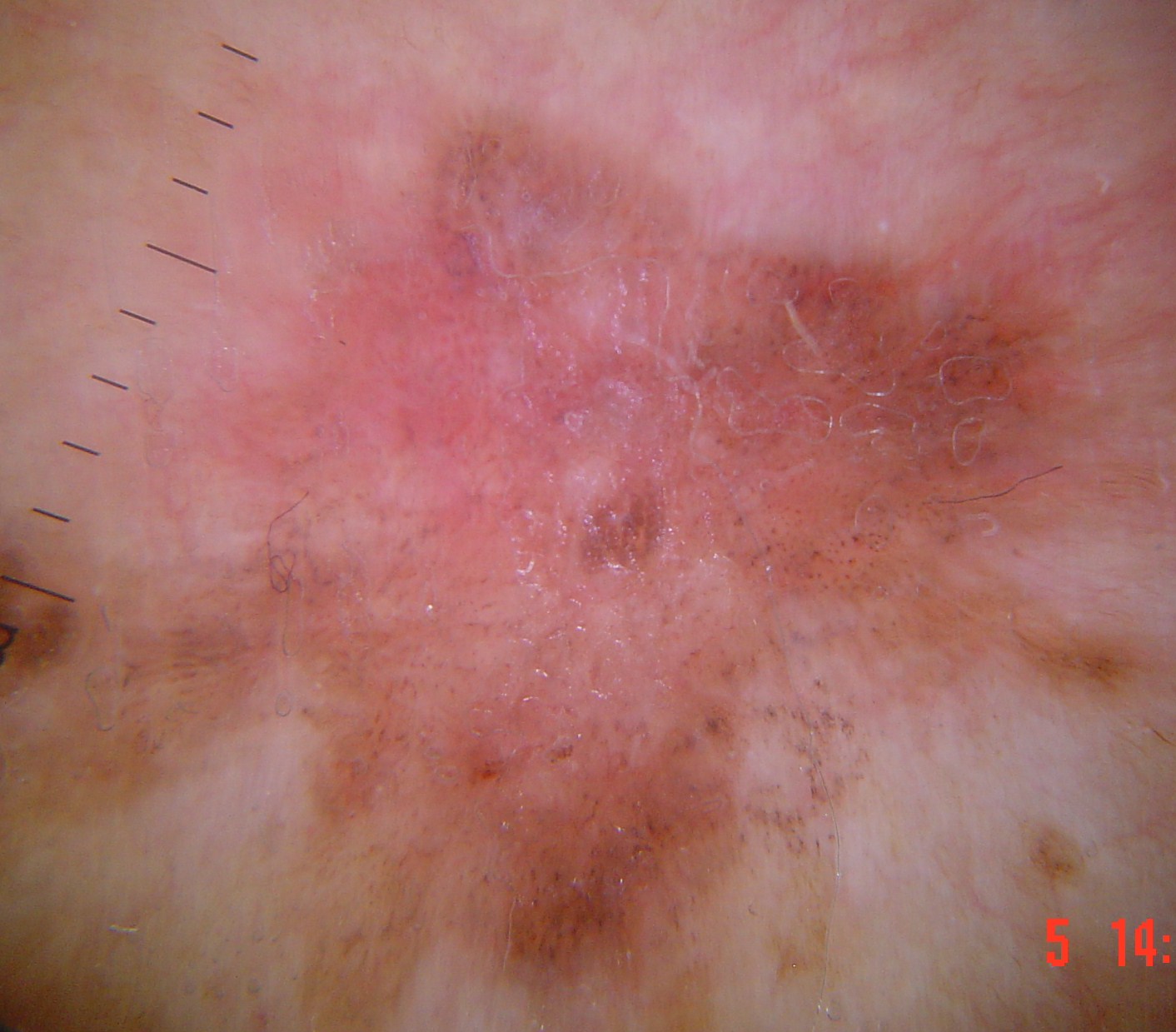Q: What is the imaging modality?
A: dermoscopy
Q: How is the lesion classified?
A: keratinocytic
Q: What did the workup show?
A: Bowen's disease (biopsy-proven)